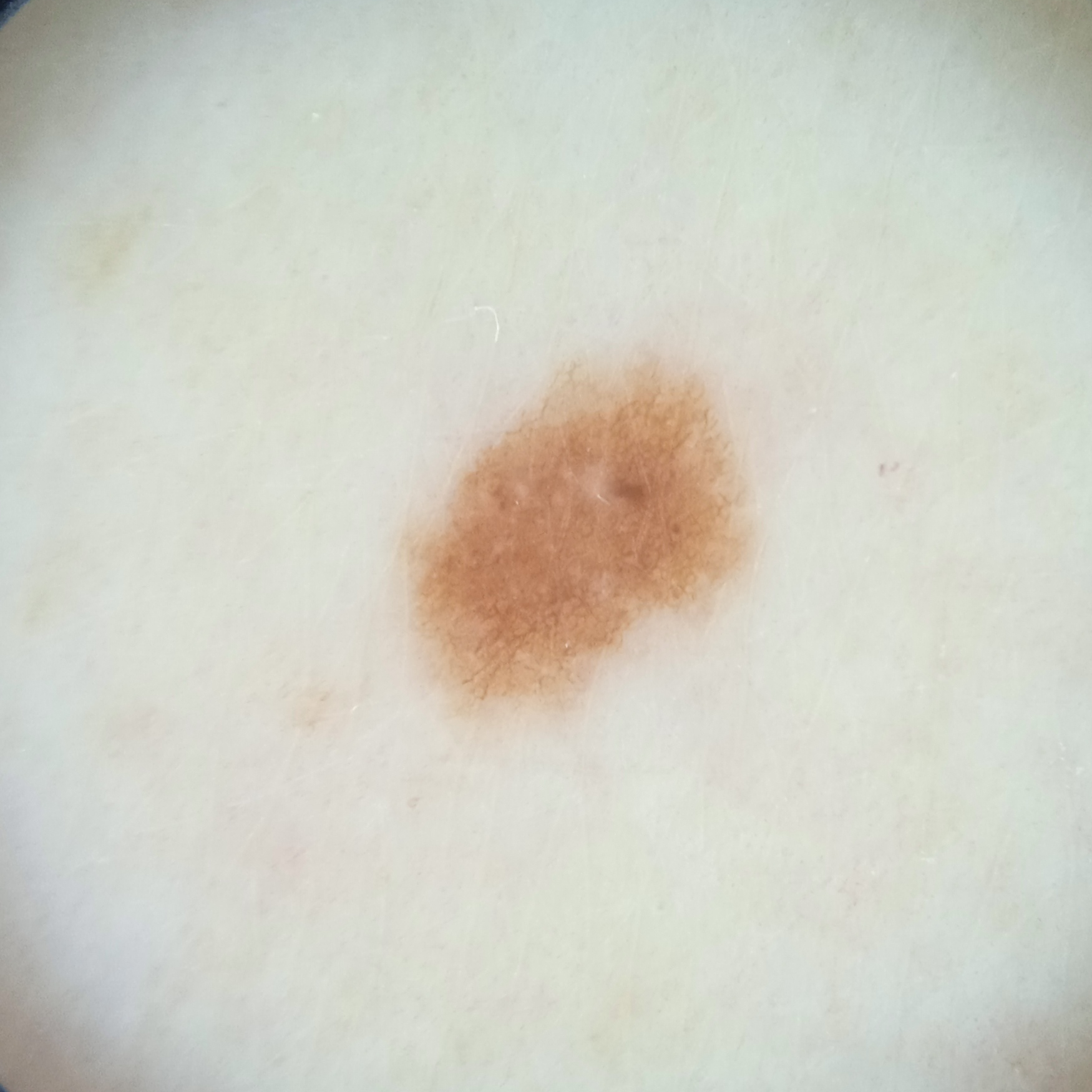The patient says their skin tans without first burning. A skin lesion imaged with a dermatoscope. The patient describes having few moles overall. A female subject aged 67. The lesion involves an arm. The lesion is about 4.9 mm across. The diagnostic impression was a melanocytic nevus.